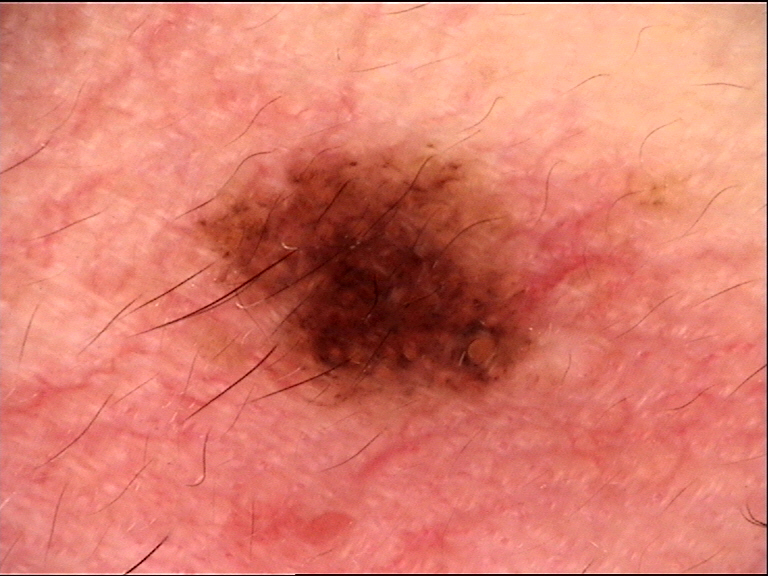<lesion>
  <diagnosis>
    <name>compound nevus</name>
    <code>cb</code>
    <malignancy>benign</malignancy>
    <super_class>melanocytic</super_class>
    <confirmation>expert consensus</confirmation>
  </diagnosis>
</lesion>